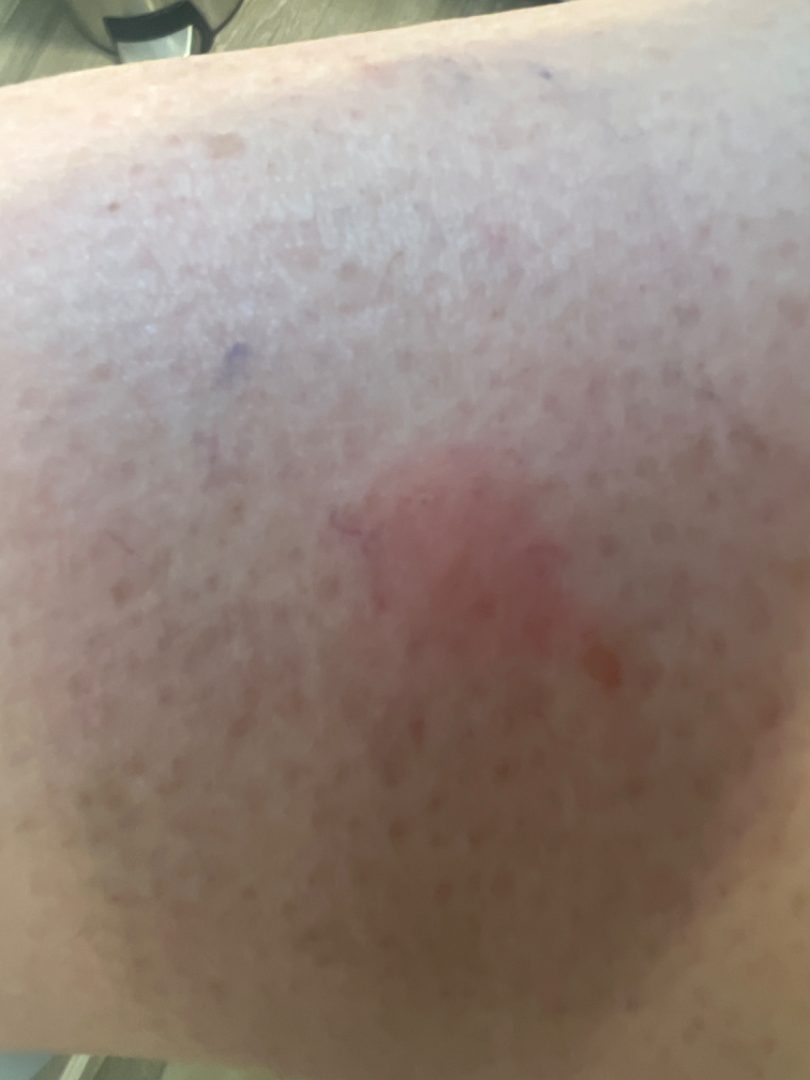On teledermatology review: Insect Bite (100%).